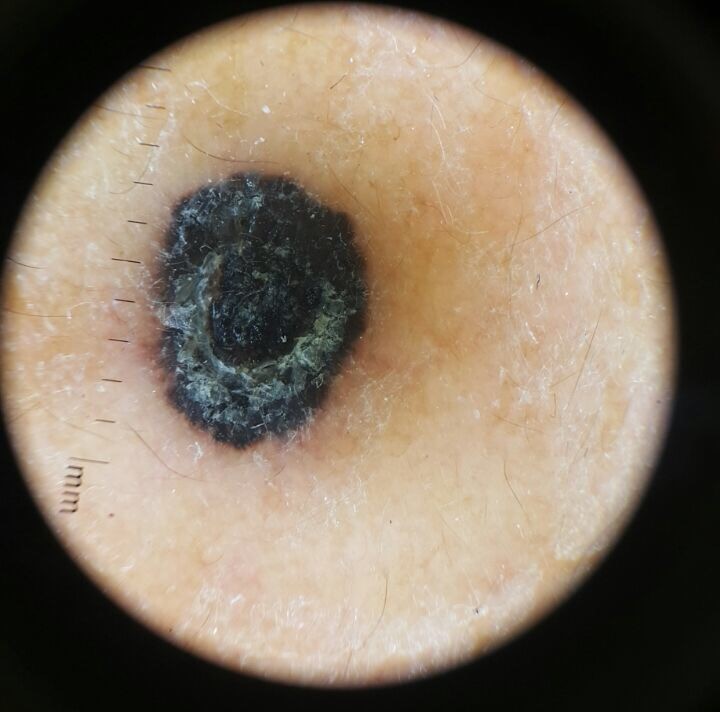diagnostic label: melanoma (biopsy-proven).